A dermatoscopic image of a skin lesion: 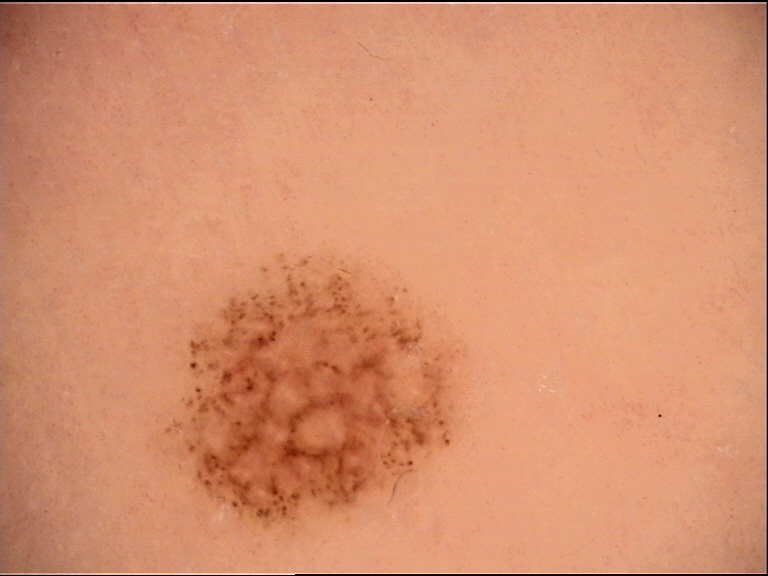Impression:
Classified as a benign lesion — an acral dysplastic junctional nevus.